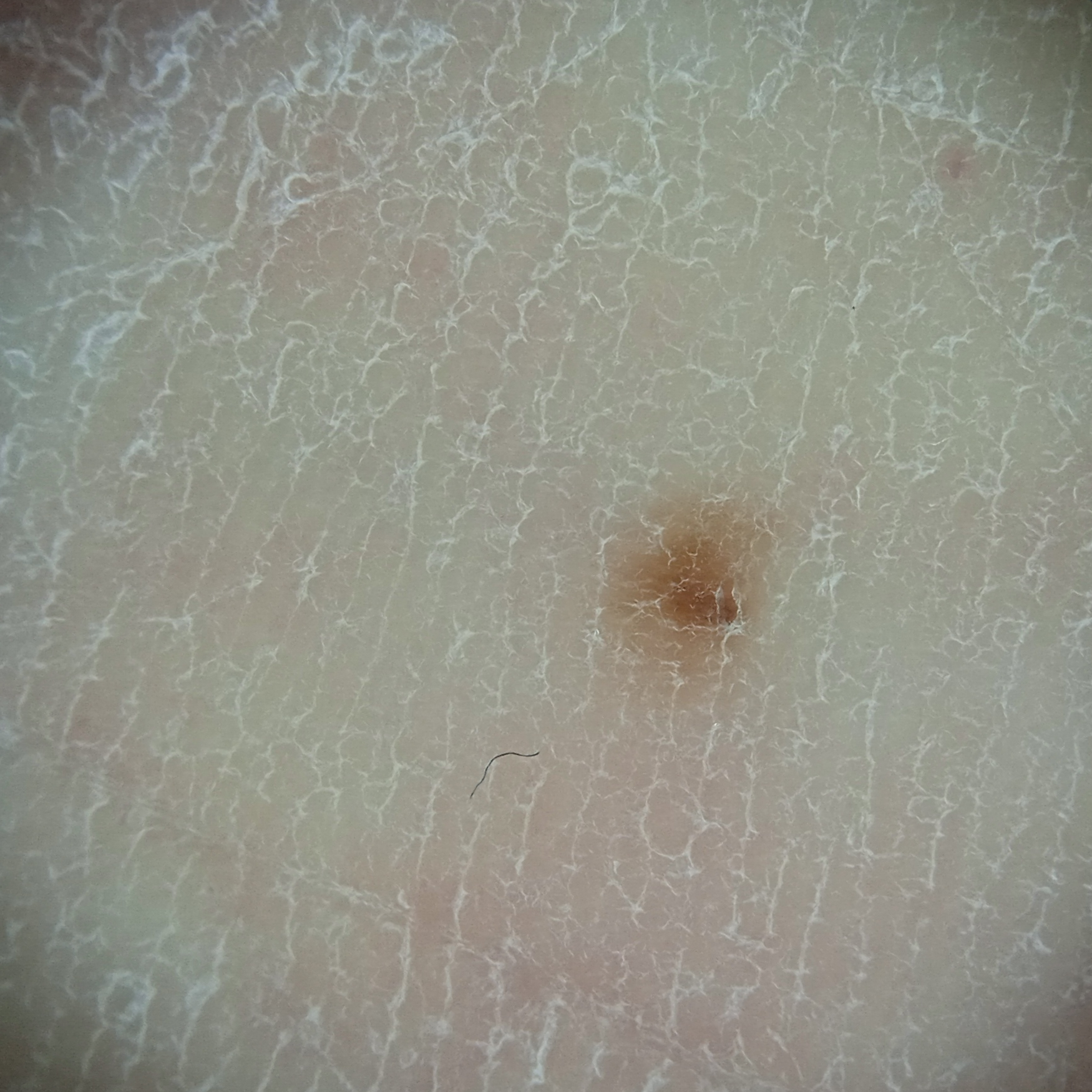Impression:
Dermatologist review favored a melanocytic nevus.